The photo was captured at a distance; located on the top or side of the foot and leg — 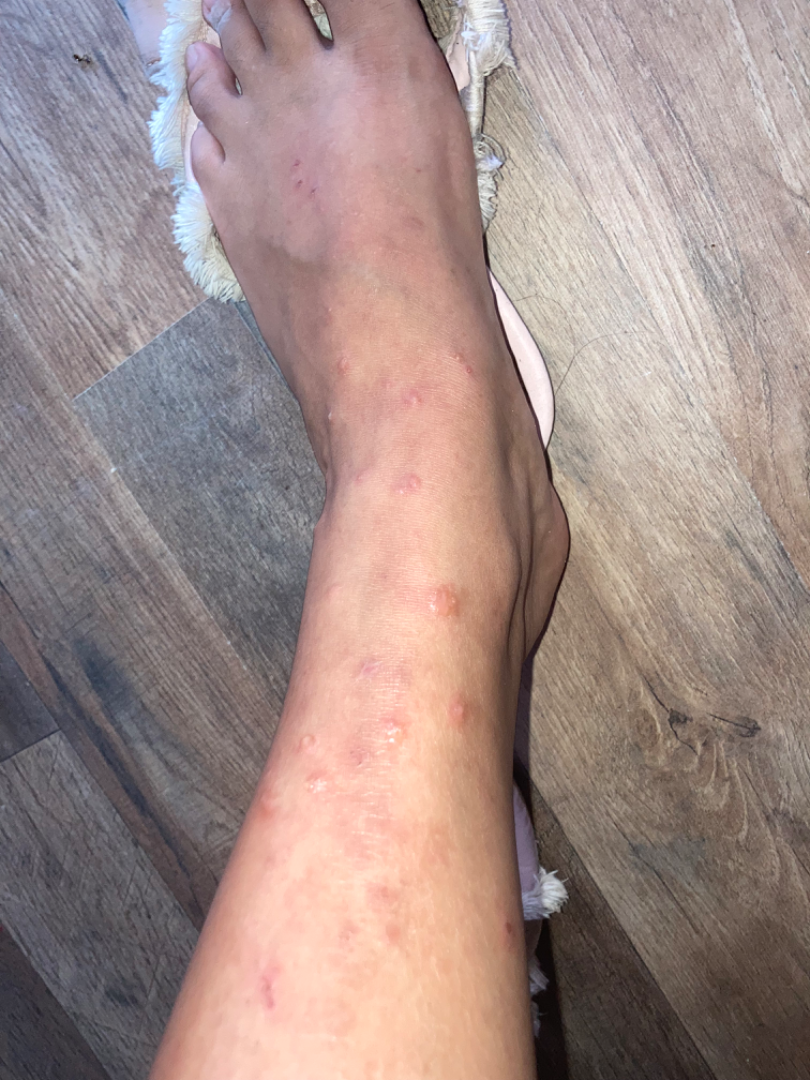On dermatologist assessment of the image, the primary impression is Insect Bite; possibly Scabies; the differential also includes Allergic Contact Dermatitis.